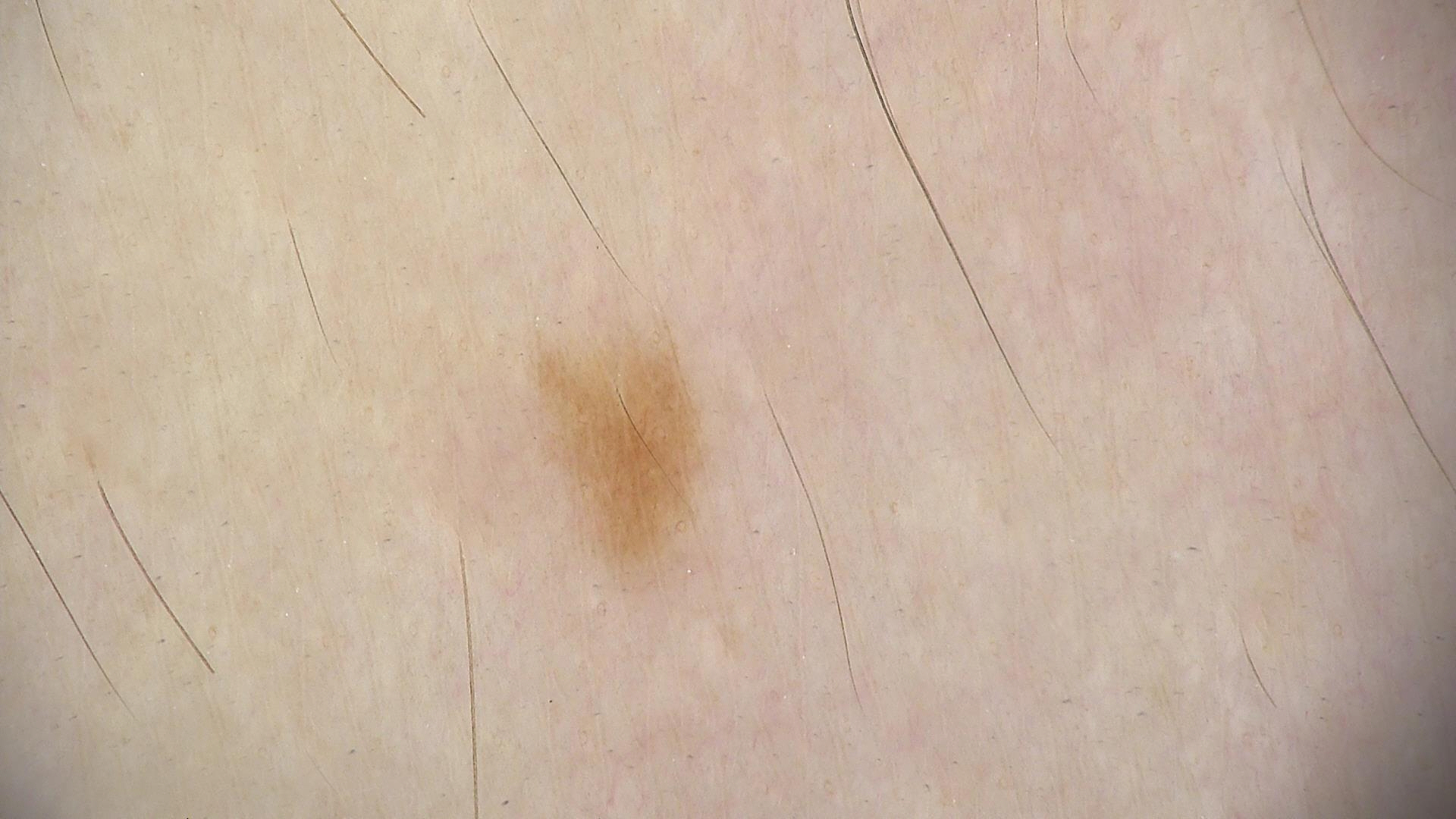A skin lesion imaged with a dermatoscope. The diagnosis was a dysplastic junctional nevus.